The head or neck, front of the torso and back of the torso are involved. The patient indicates the condition has been present for about one day. The photo was captured at an angle. The lesion is described as raised or bumpy — 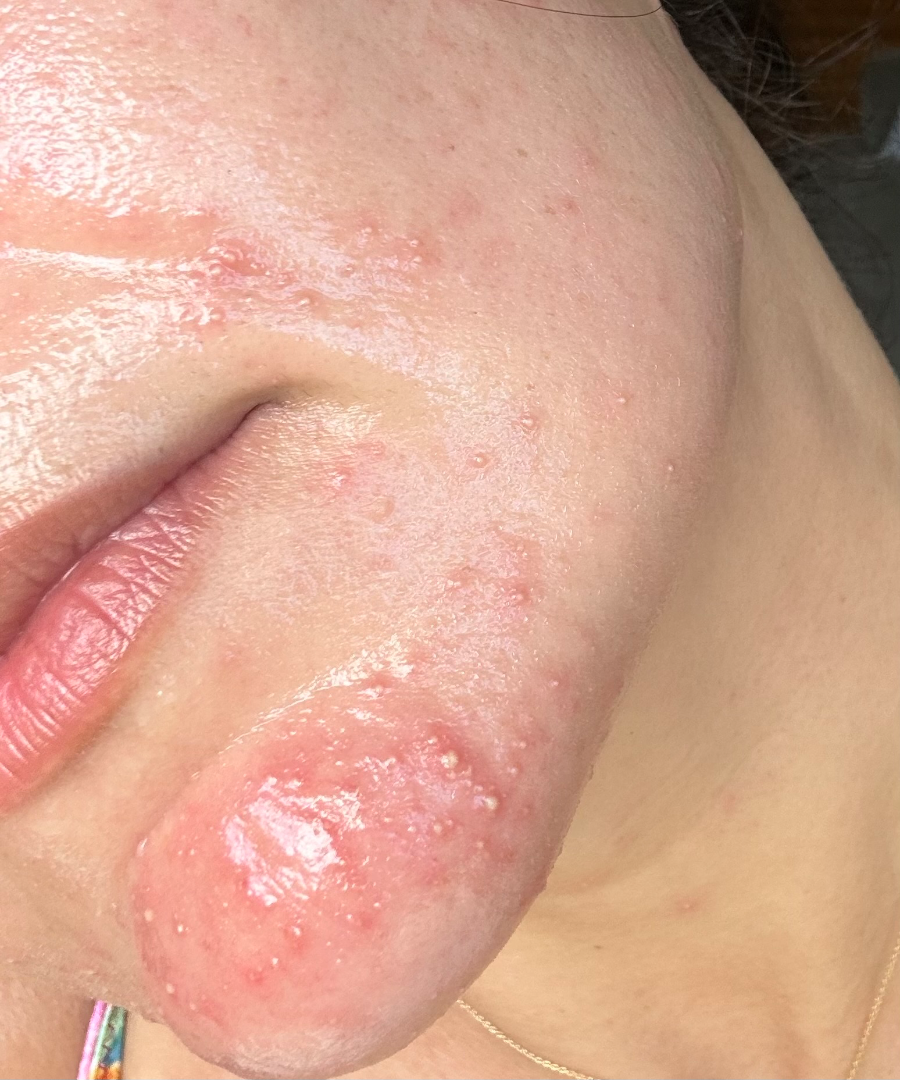Case summary:
– differential diagnosis: Rosacea and Perioral Dermatitis were considered with similar weight